A dermoscopic close-up of a skin lesion.
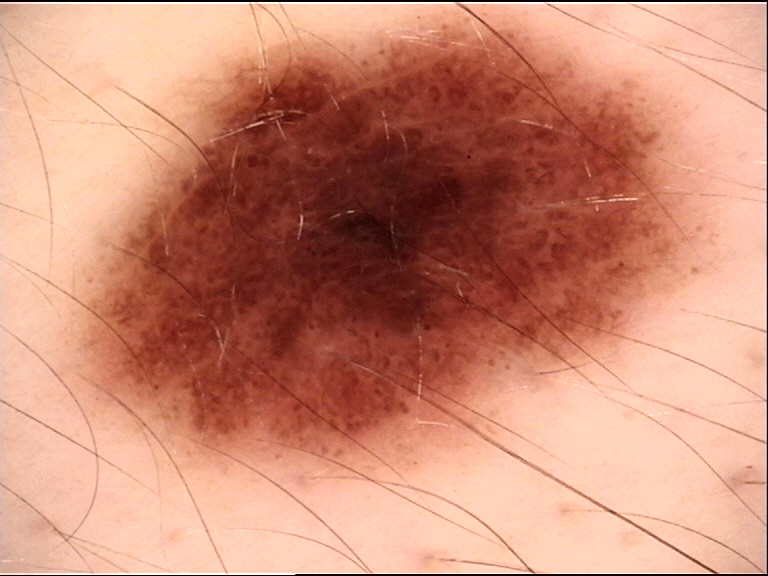The diagnosis was a dysplastic compound nevus.